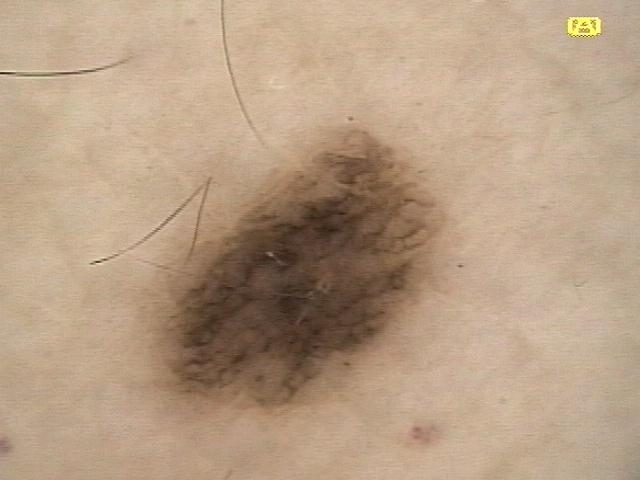Q: Who is the patient?
A: male, about 80 years old
Q: What kind of image is this?
A: dermatoscopic image
Q: Skin phototype?
A: II
Q: Where on the body is the lesion?
A: the posterior trunk
Q: What was the clinical impression?
A: Nevus